Self-categorized by the patient as skin that appeared healthy to them; symptoms reported: bothersome appearance; a close-up photograph; present for about one day; skin tone: Fitzpatrick II; texture is reported as flat; the affected area is the arm and front of the torso; the patient is male: 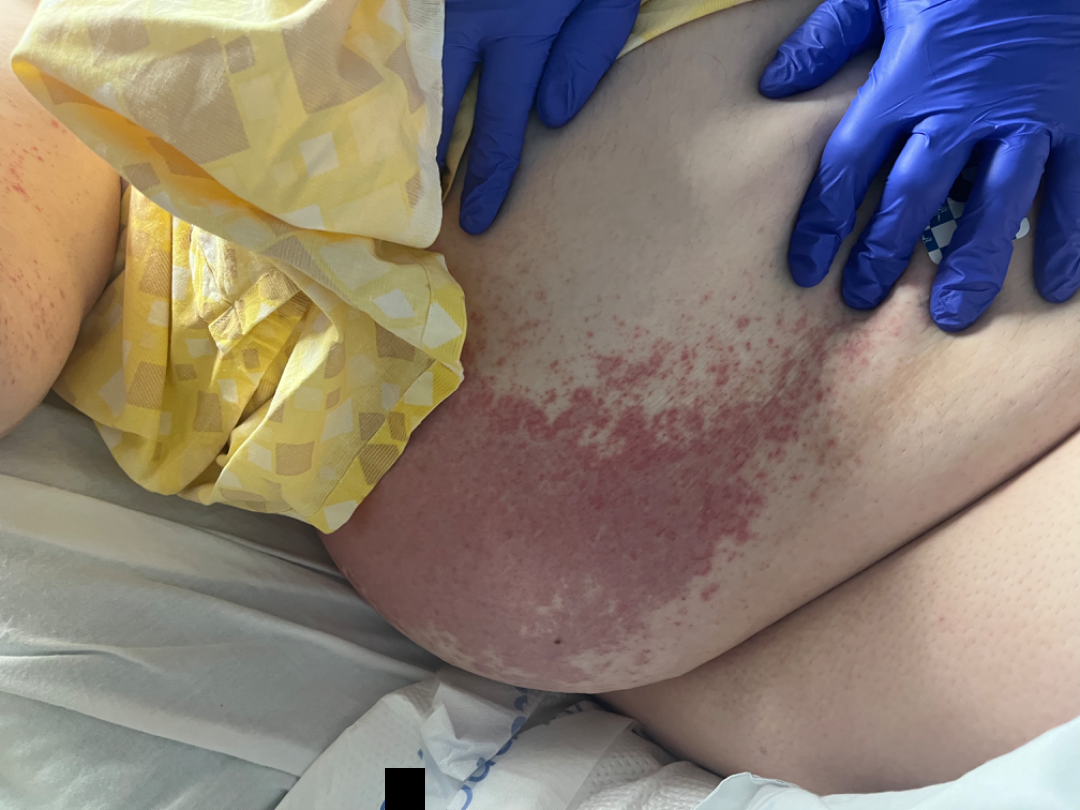Notes:
* differential diagnosis · Herpes Zoster, Hypersensitivity and Allergic Contact Dermatitis were considered with similar weight